The patient is a female aged 60–69. The lesion involves the arm. The photo was captured at an angle.
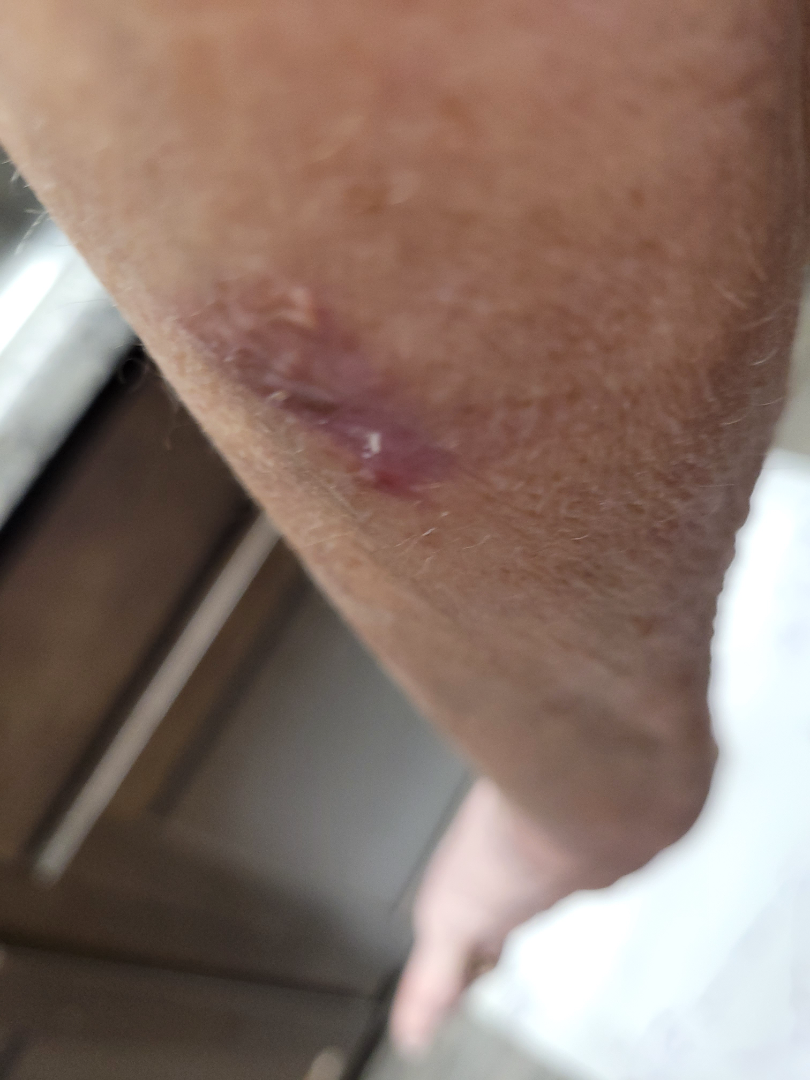Review: Reviewed remotely by three dermatologists: the impression is Scar Condition.